A skin lesion imaged with a dermatoscope.
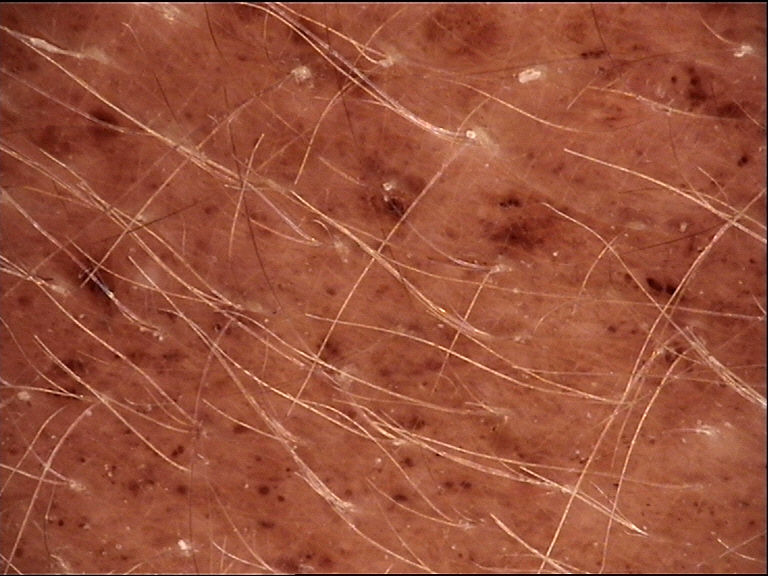diagnosis=congenital compound nevus (expert consensus).